The patient is 18–29, female · the affected area is the front of the torso, arm and leg · a close-up photograph — 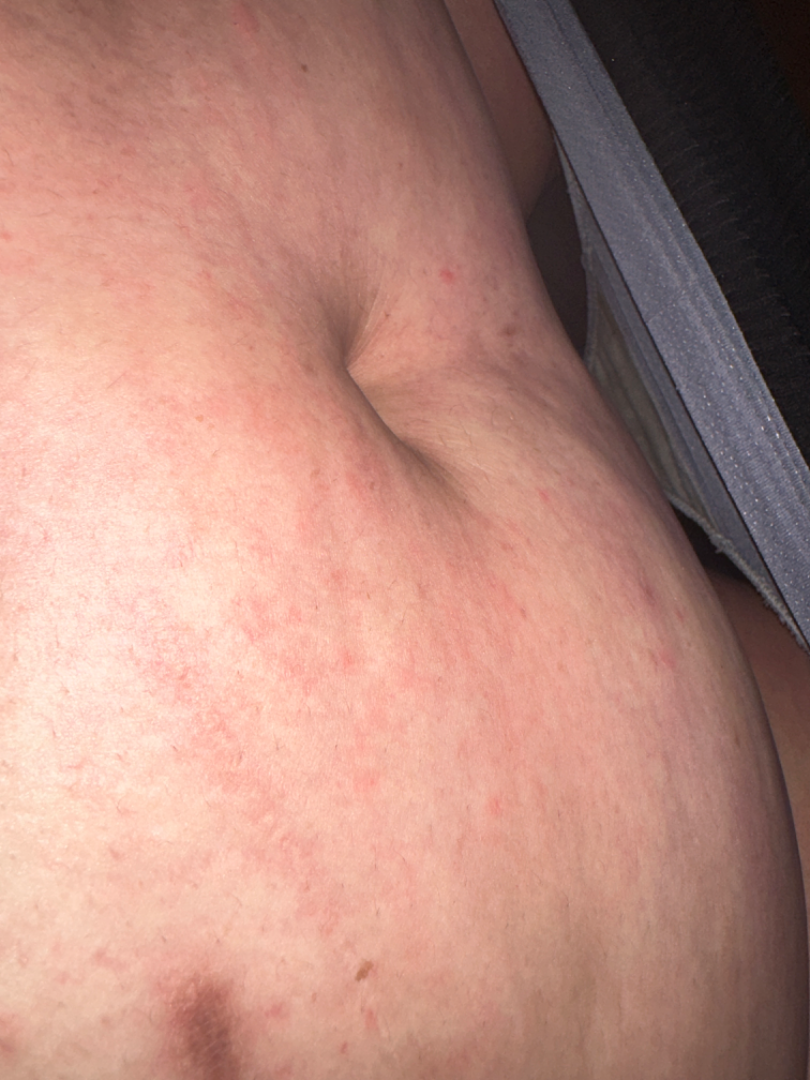Q: What is the dermatologist's impression?
A: reviewed remotely by three dermatologists: in keeping with Contact dermatitis